A dermoscopic image of a skin lesion:
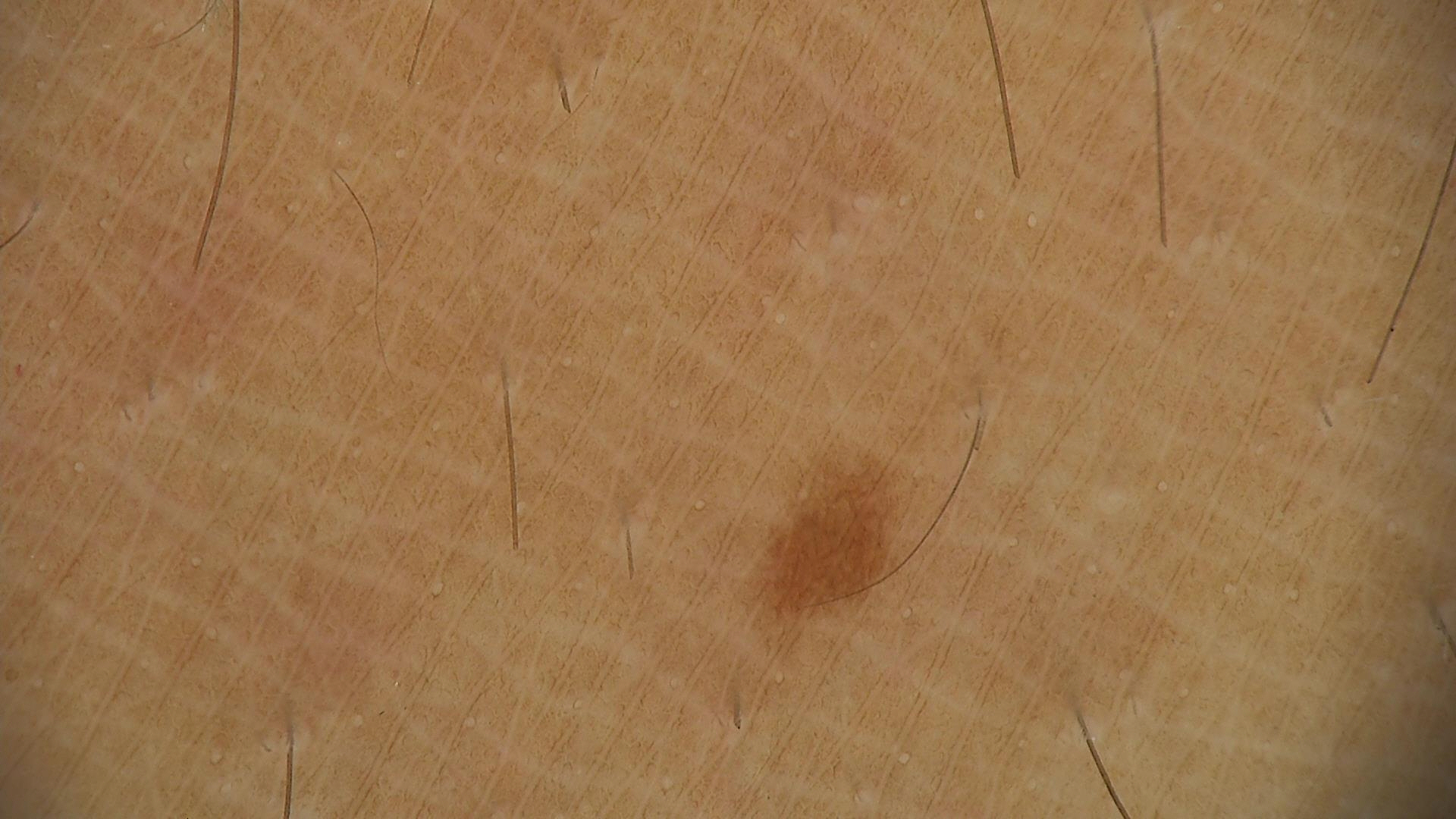diagnosis = junctional nevus (expert consensus).